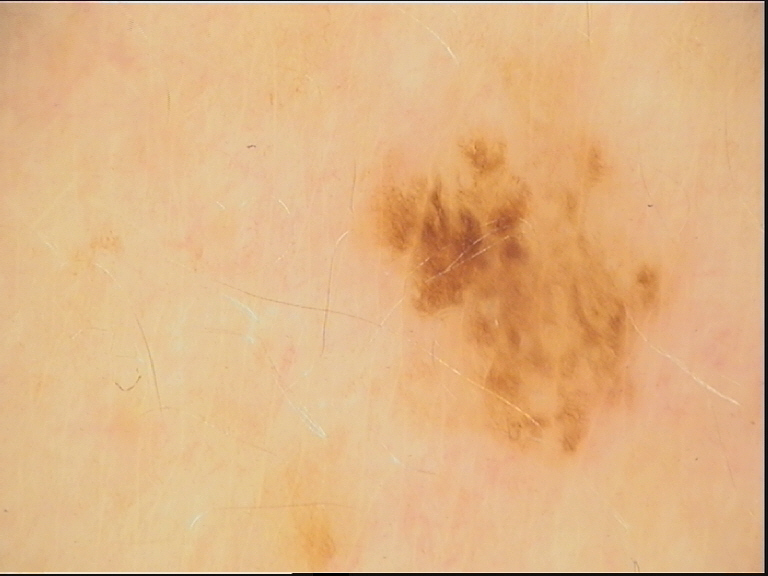Conclusion:
Labeled as a dysplastic junctional nevus.